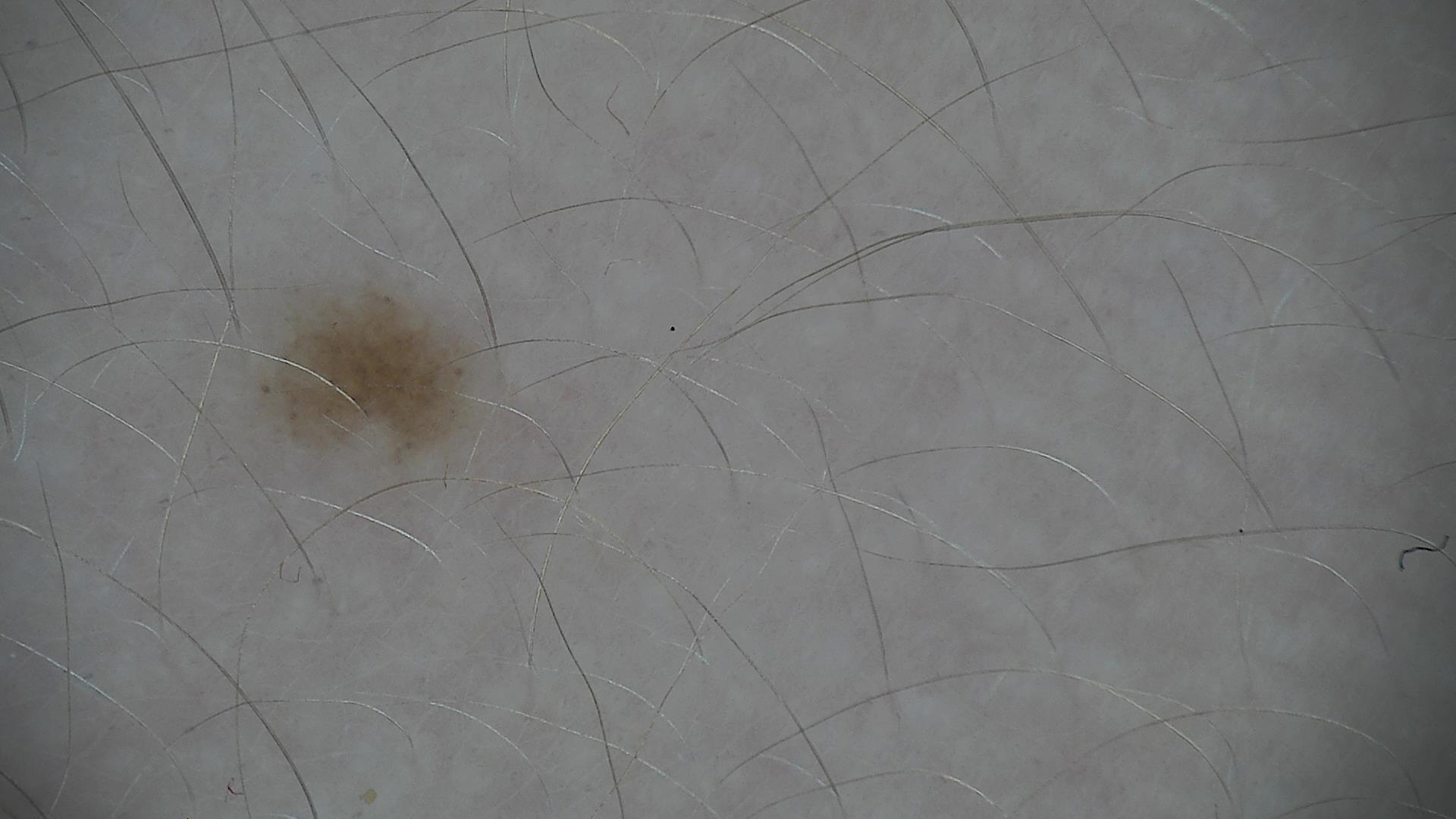| field | value |
|---|---|
| class | dysplastic junctional nevus (expert consensus) |